A female patient aged 80; history notes prior skin cancer (patient or family); FST I; a clinical close-up photograph of a skin lesion — 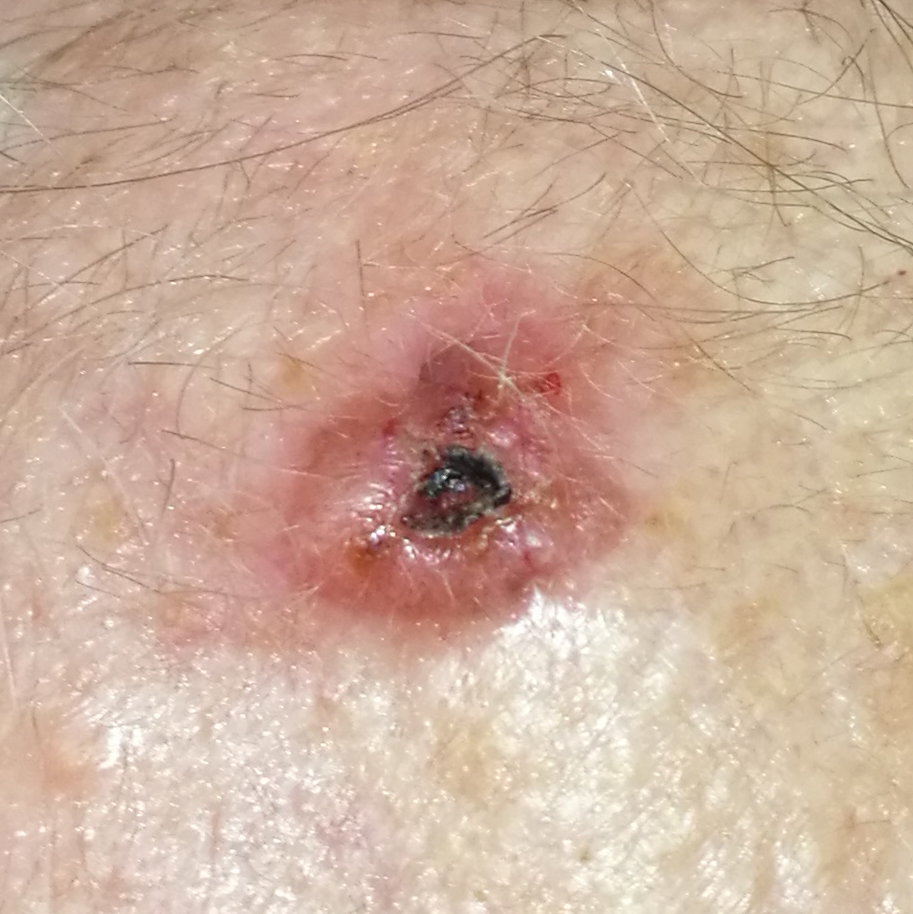Q: What is the anatomic site?
A: the face
Q: What symptoms does the patient report?
A: growth, itching, elevation, bleeding / no pain
Q: What is the diagnosis?
A: basal cell carcinoma (biopsy-proven)